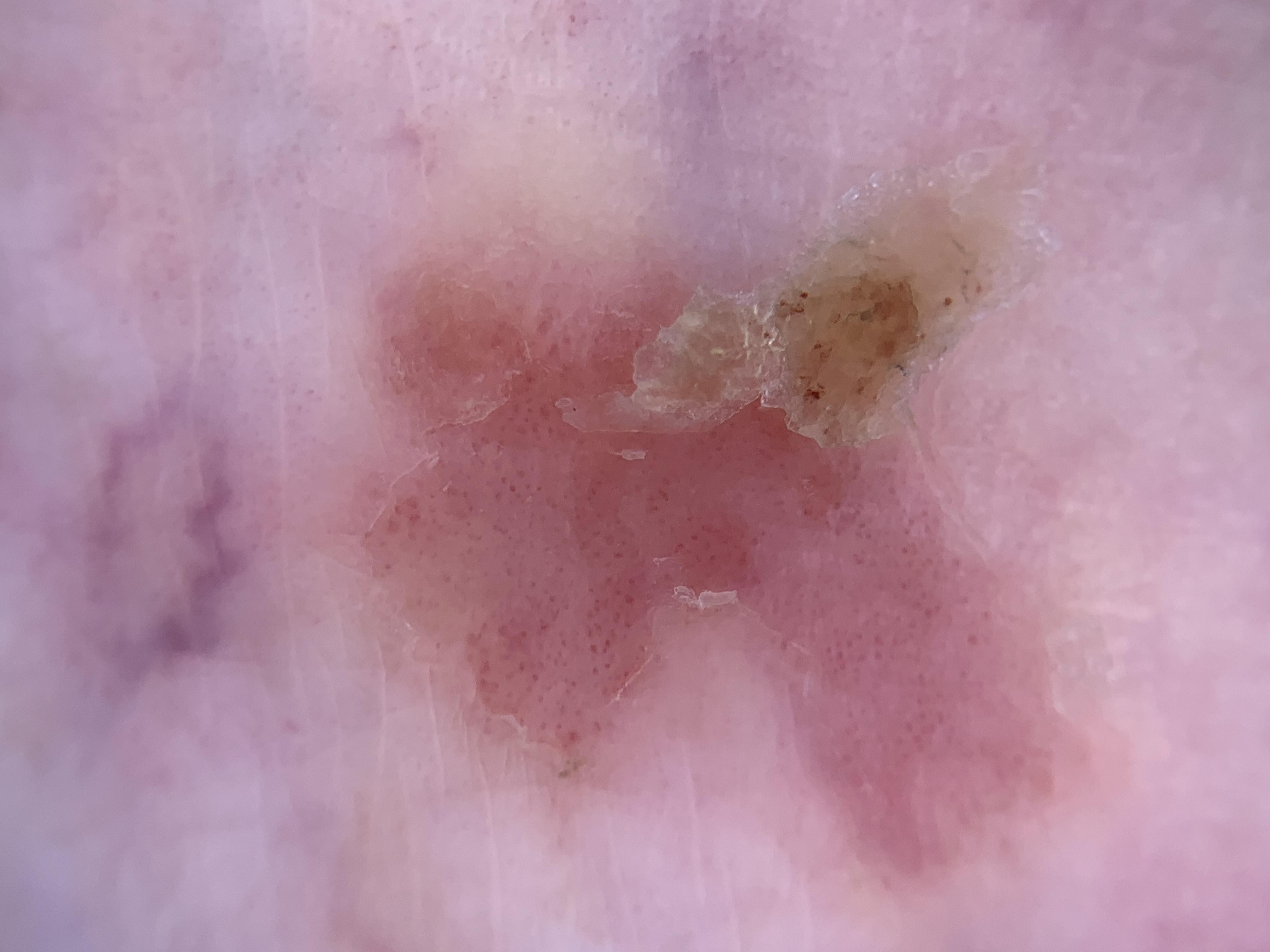A dermoscopic image of a skin lesion. A female patient about 75 years old. The lesion involves a lower extremity. On biopsy, the diagnosis was a squamous cell carcinoma.